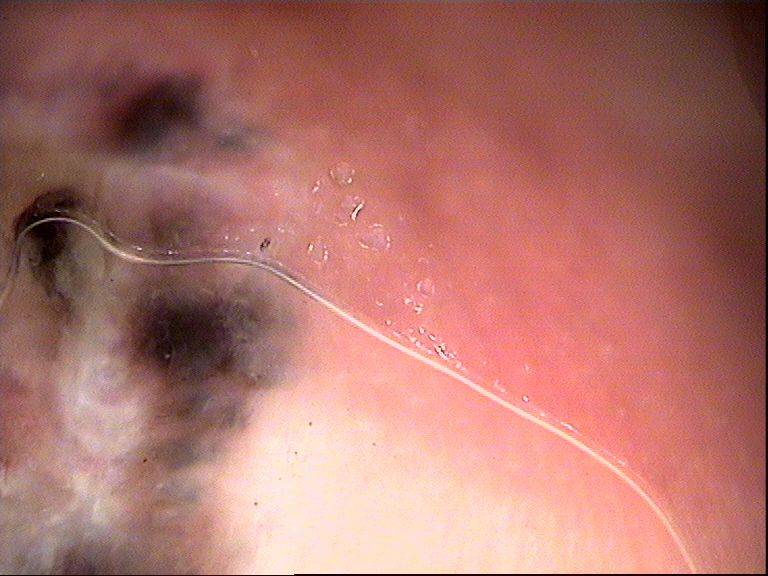Histopathology confirmed an acral nodular melanoma.